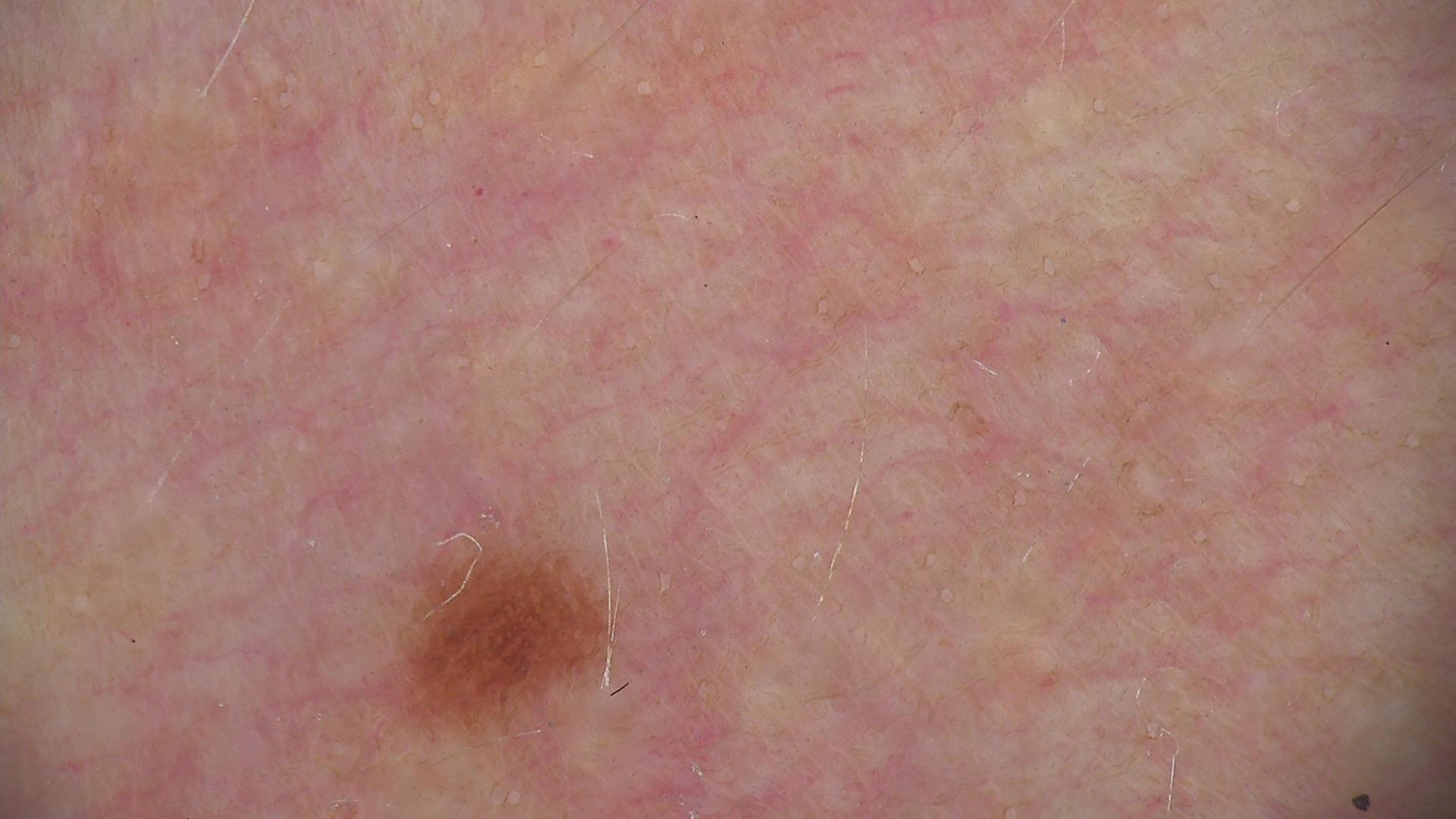The diagnosis was a junctional nevus.